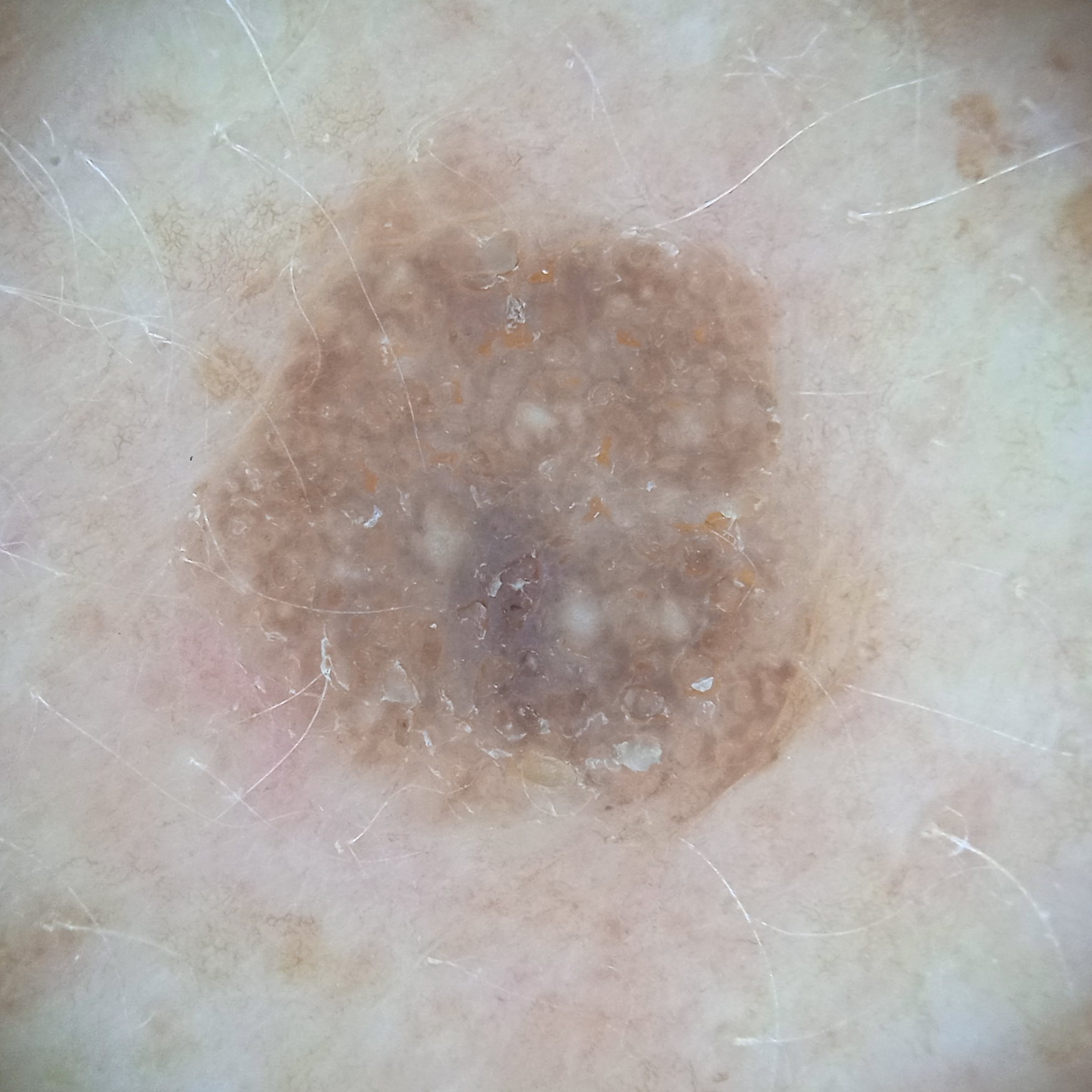Findings:
Collected as part of a research study, without a referral diagnosis. The patient says their skin tans without first burning. A female subject 78 years of age. The lesion is about 7.3 mm across.
Conclusion:
Dermatologist review favored a seborrheic keratosis.